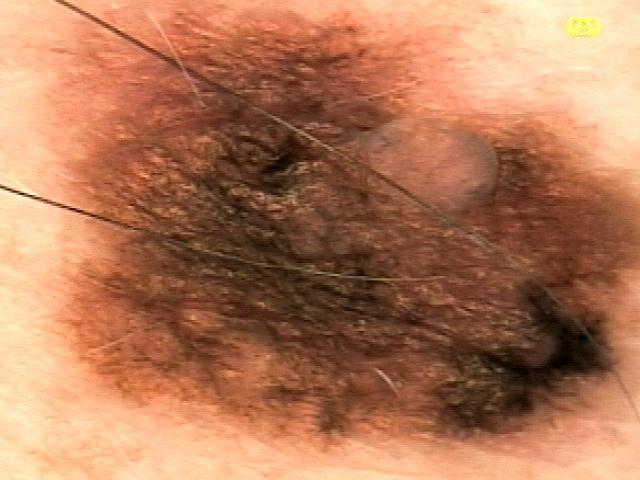| field | value |
|---|---|
| subject | male, aged 38 to 42 |
| modality | dermatoscopic image |
| diagnostic label | Melanoma (biopsy-proven) |